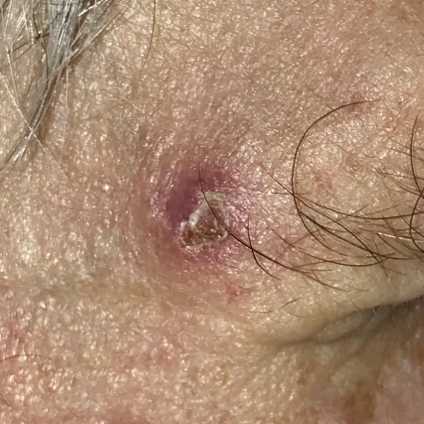Patient and lesion:
A clinical photo of a skin lesion taken with a smartphone. Located on the face. By the patient's account, the lesion has bled, is elevated, and itches.
Conclusion:
Confirmed on histopathology as a basal cell carcinoma.